Fitzpatrick IV; lay reviewers estimated 3 on the Monk Skin Tone. The patient reports bothersome appearance, itching and enlargement. The condition has been present for about one day. Texture is reported as raised or bumpy. Located on the arm. Self-categorized by the patient as a rash. An image taken at an angle:
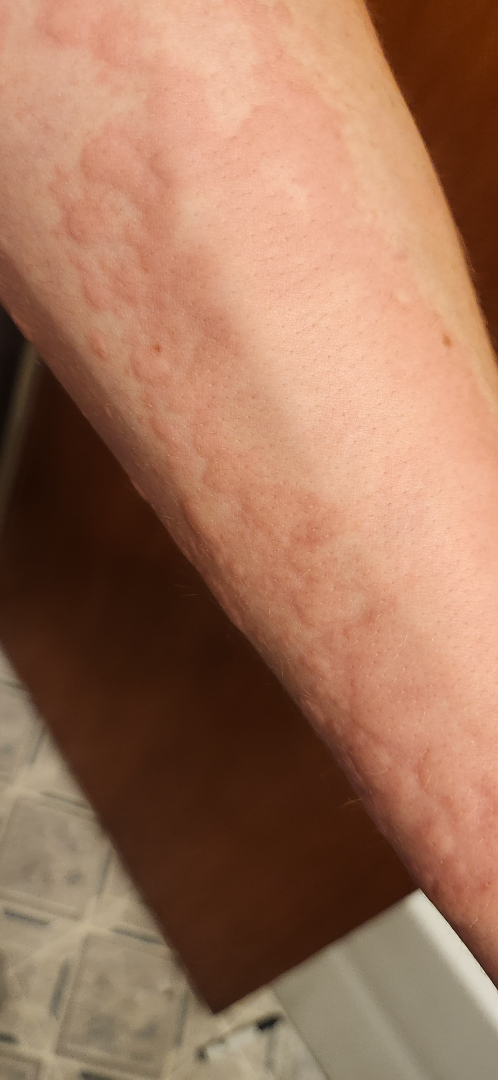{
  "differential": {
    "leading": [
      "Leukocytoclastic Vasculitis"
    ],
    "considered": [
      "Calciphylaxis cutis",
      "Erythema multiforme"
    ]
  }
}